Close-up view · the patient is a female aged 60–69 · located on the head or neck and arm: 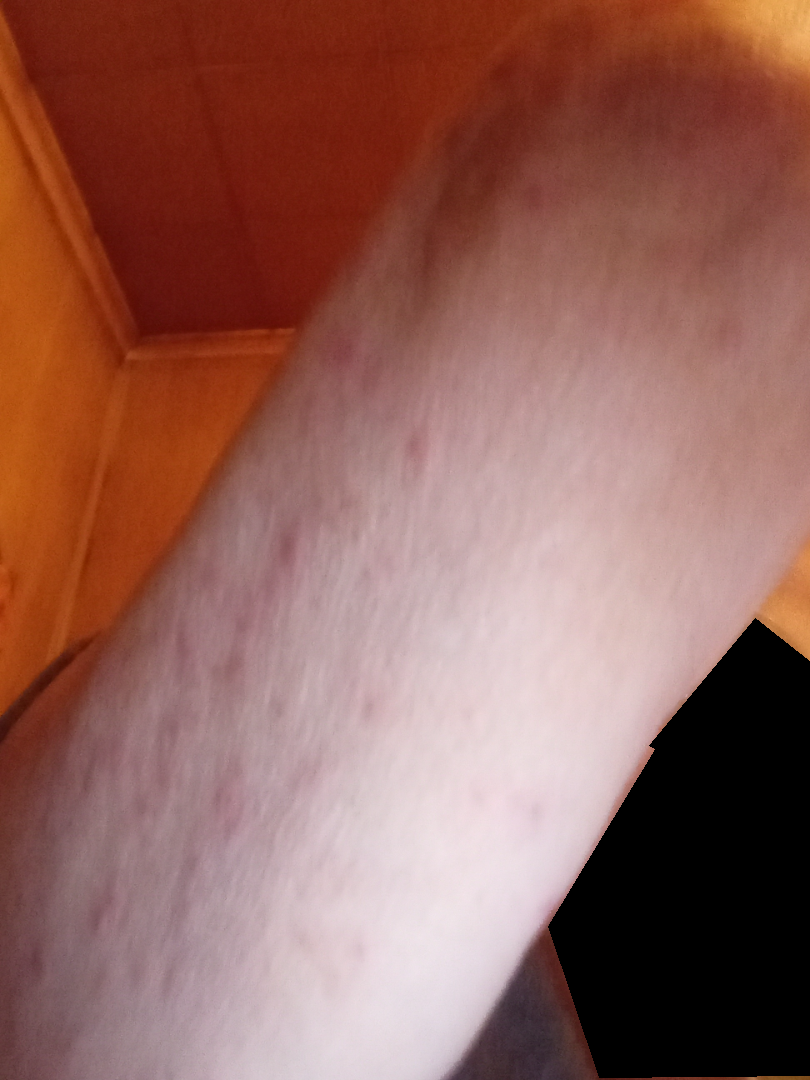Assessment: The skin condition could not be confidently assessed from this image.